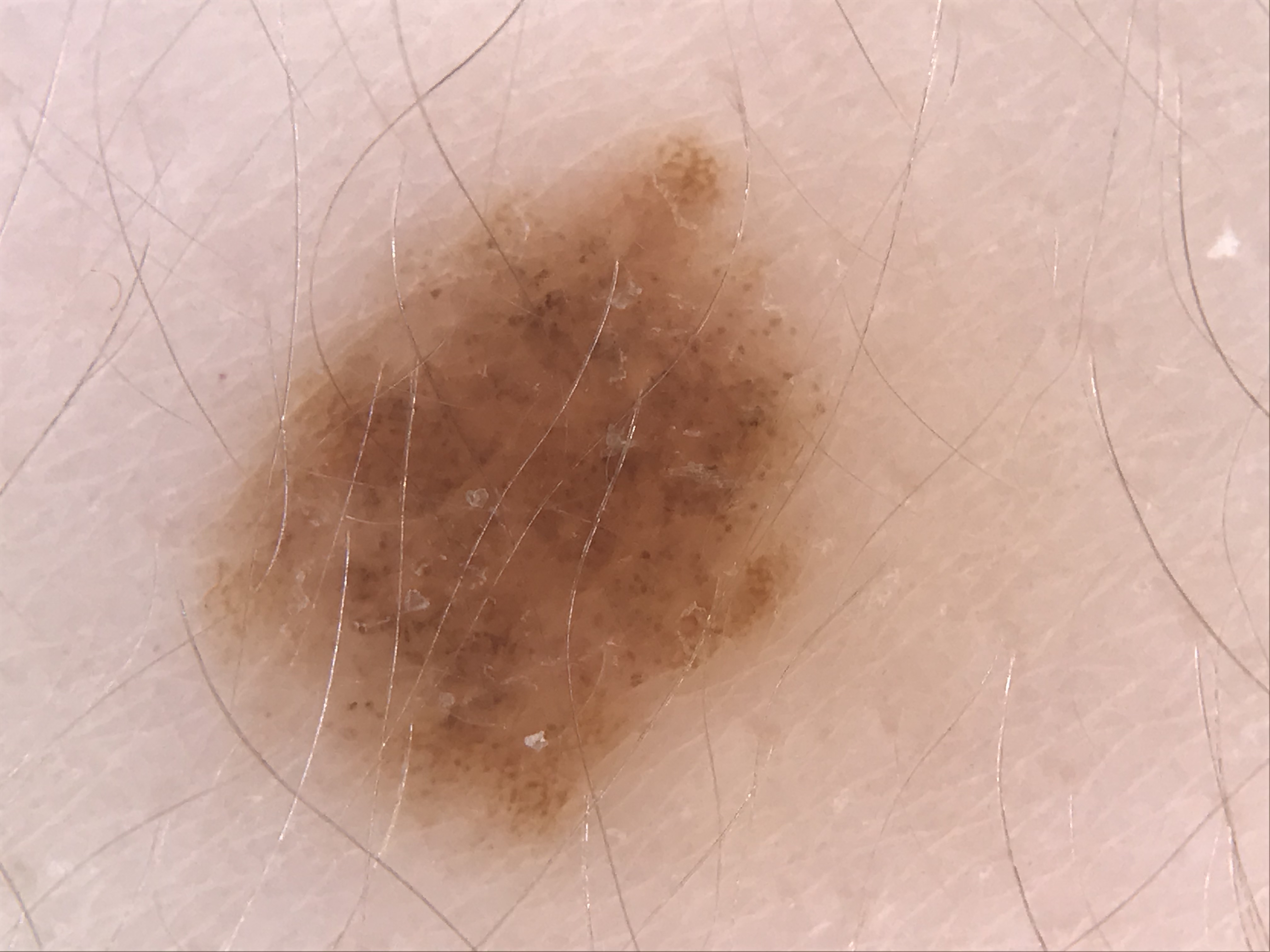A dermoscopic close-up of a skin lesion. The diagnostic label was a benign lesion — a dysplastic compound nevus.